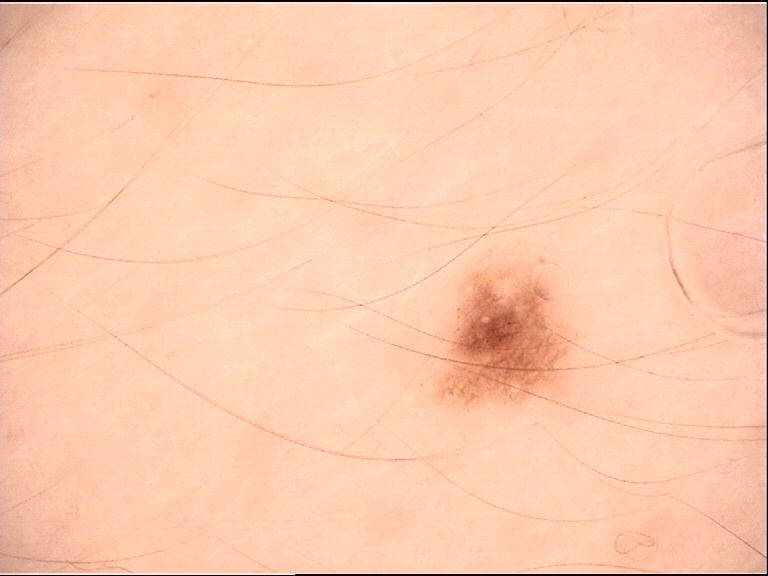  image: dermoscopy
  lesion_type:
    main_class: banal
    pattern: junctional
  diagnosis:
    name: junctional nevus
    code: jb
    malignancy: benign
    super_class: melanocytic
    confirmation: expert consensus